A dermoscopy image of a single skin lesion.
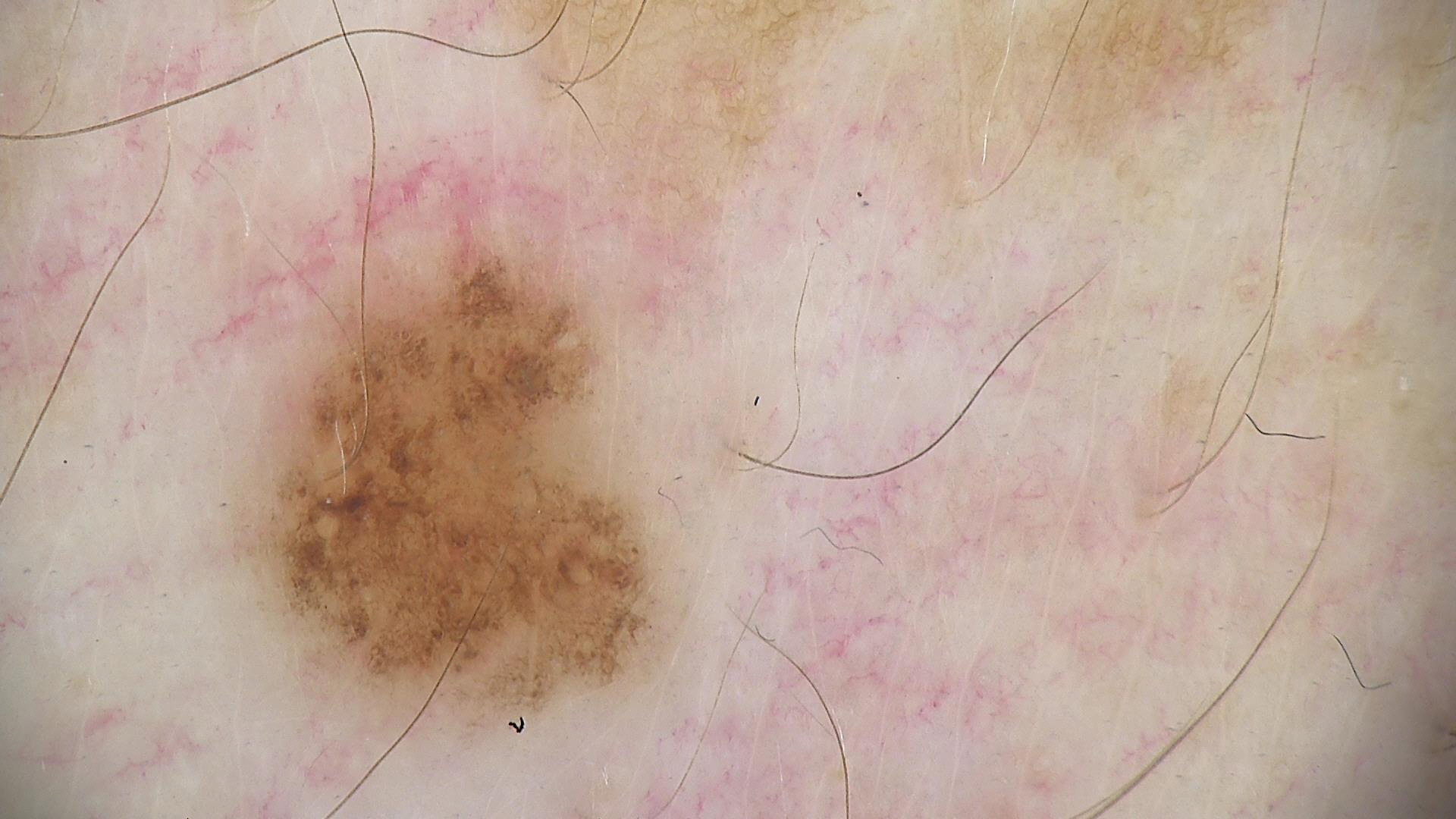Consistent with a dysplastic junctional nevus.